FST V. The patient reports the lesion is raised or bumpy. Close-up view. The contributor is a female aged 40–49. The condition has been present for less than one week.
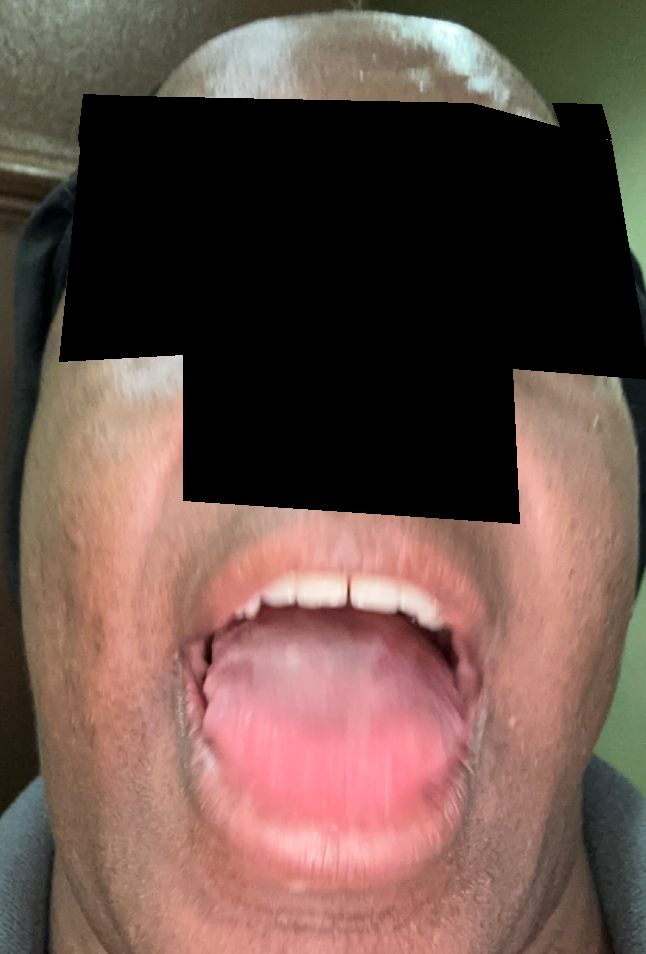On photographic review, favoring Geographic tongue; the differential also includes Atrophic glossitis; with consideration of Lichen planus/lichenoid eruption.